A female patient aged 58. The chart notes prior skin cancer (patient or family) and pesticide exposure. A smartphone photograph of a skin lesion:
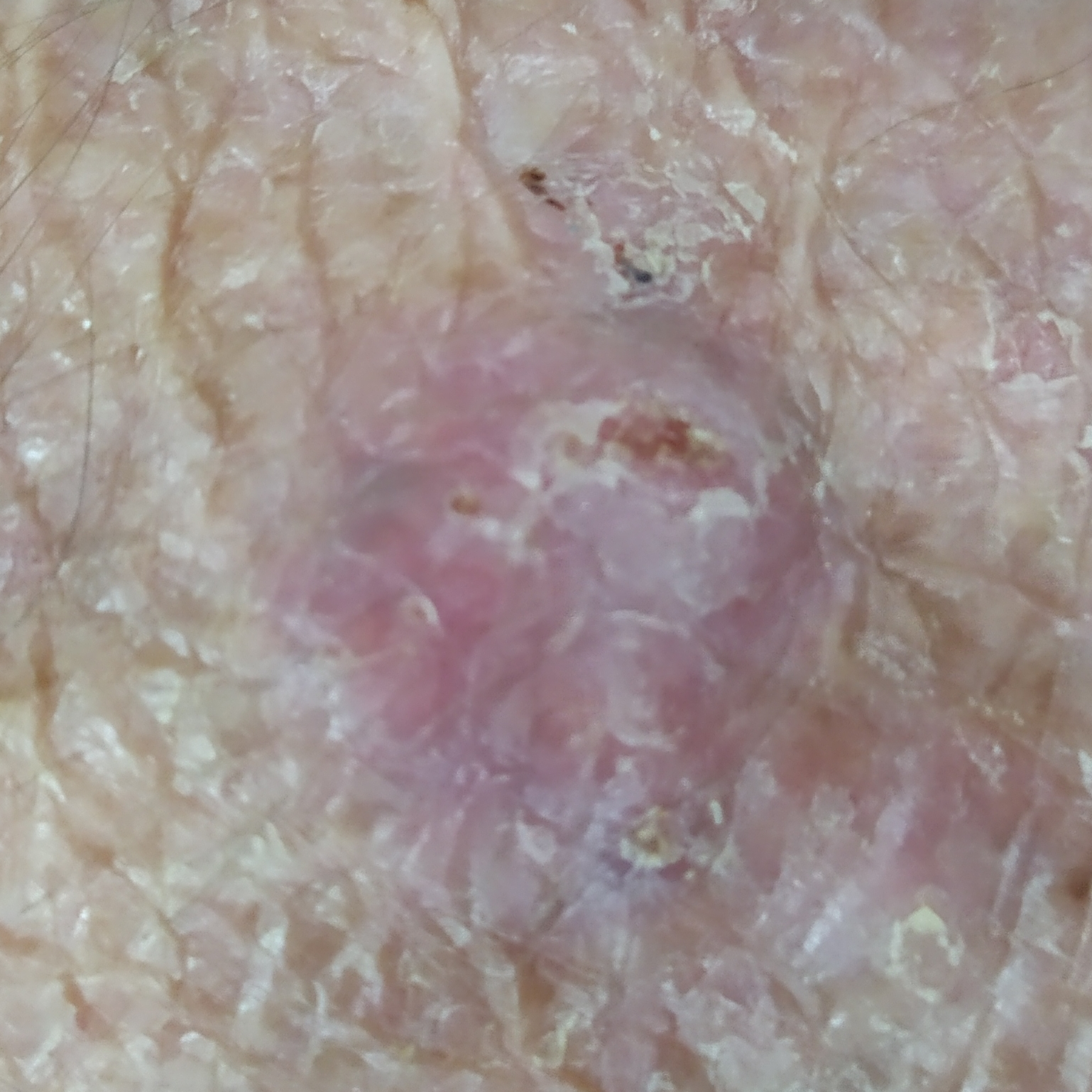lesion_location: a hand
lesion_size:
  diameter_1_mm: 16.0
  diameter_2_mm: 13.0
symptoms:
  present:
    - elevation
    - bleeding
    - itching
    - growth
diagnosis:
  name: basal cell carcinoma
  code: BCC
  malignancy: malignant
  confirmation: histopathology